A male subject 64 years old. The patient was assessed as Fitzpatrick II. A clinical photo of a skin lesion taken with a smartphone. The chart notes prior skin cancer (patient or family), tobacco use, pesticide exposure, and prior malignancy (patient or family): 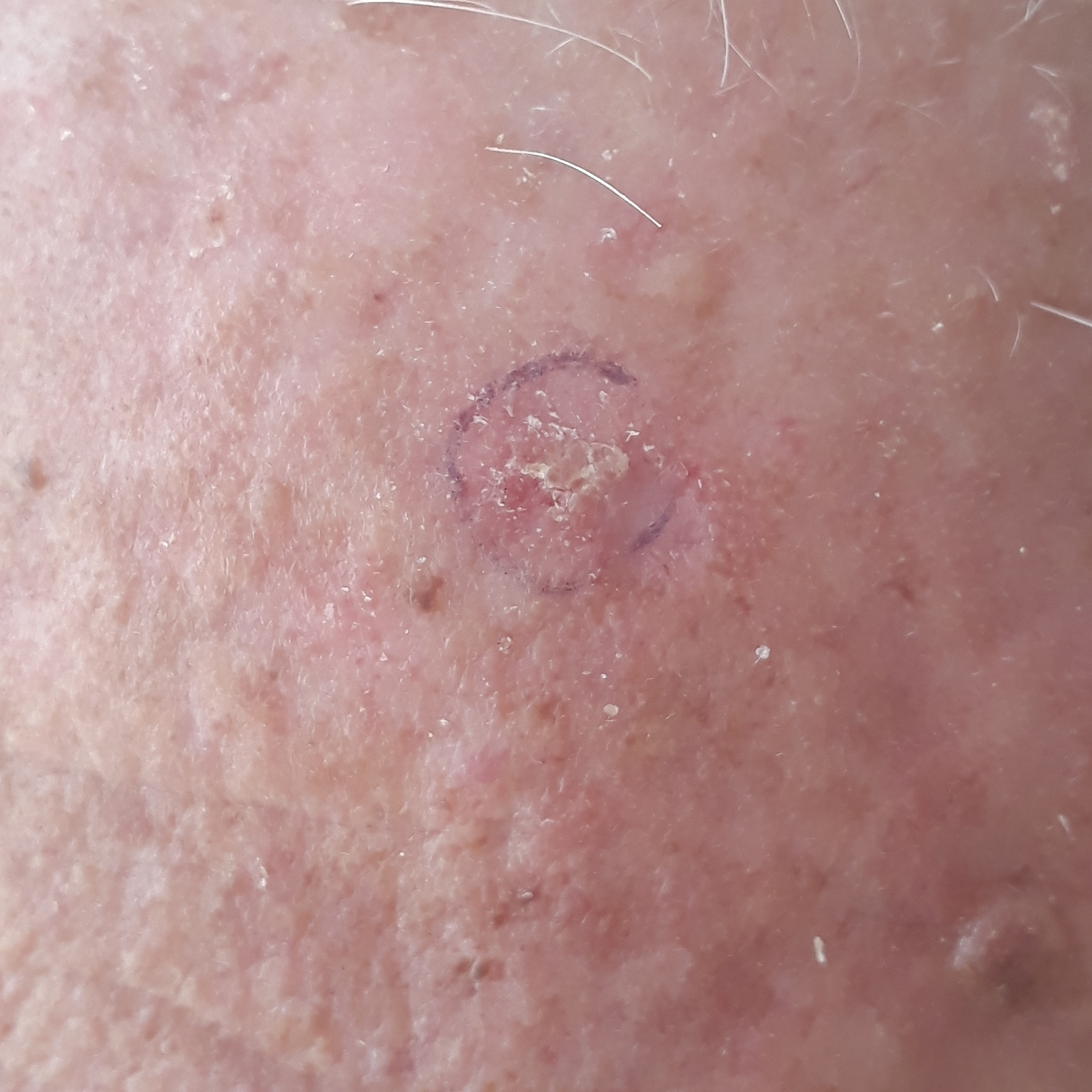<skin_lesion>
<lesion_location>the face</lesion_location>
<lesion_size>
<diameter_1_mm>10.0</diameter_1_mm>
<diameter_2_mm>10.0</diameter_2_mm>
</lesion_size>
<symptoms>
<present>itching</present>
<absent>pain</absent>
</symptoms>
<diagnosis>
<name>actinic keratosis</name>
<code>ACK</code>
<malignancy>indeterminate</malignancy>
<confirmation>clinical consensus</confirmation>
</diagnosis>
</skin_lesion>